The lesion involves the arm, the photograph was taken at a distance: 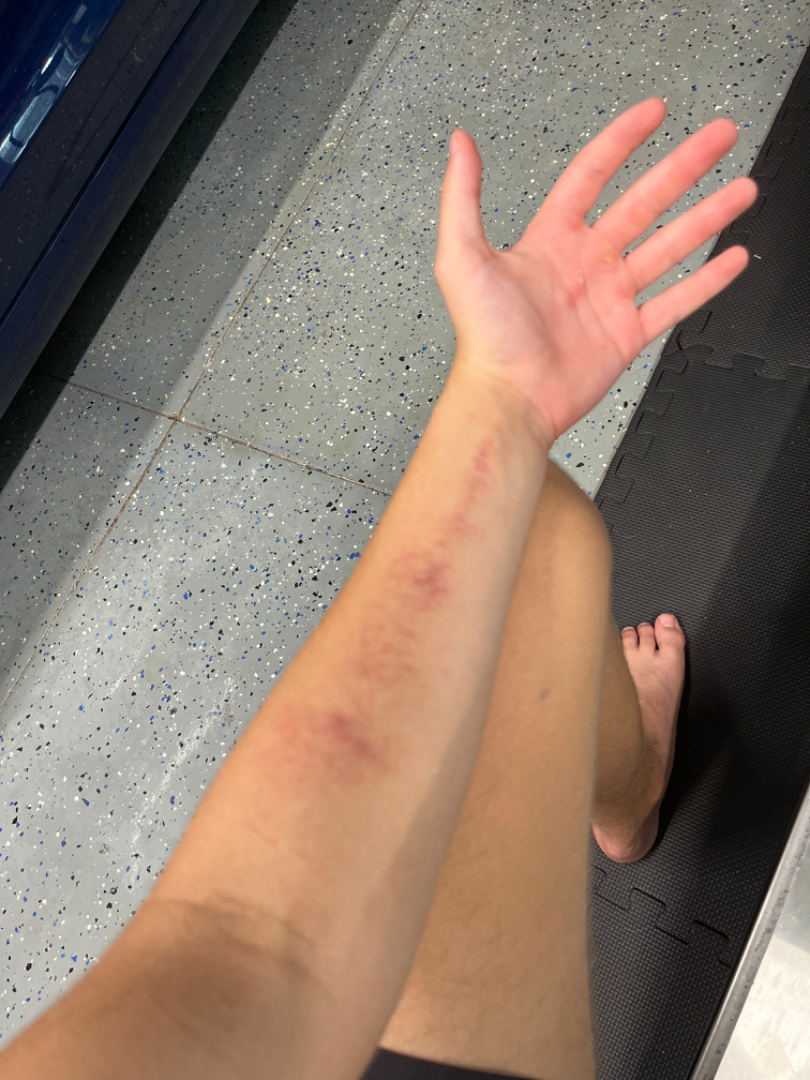Q: What was the assessment?
A: indeterminate from the photograph